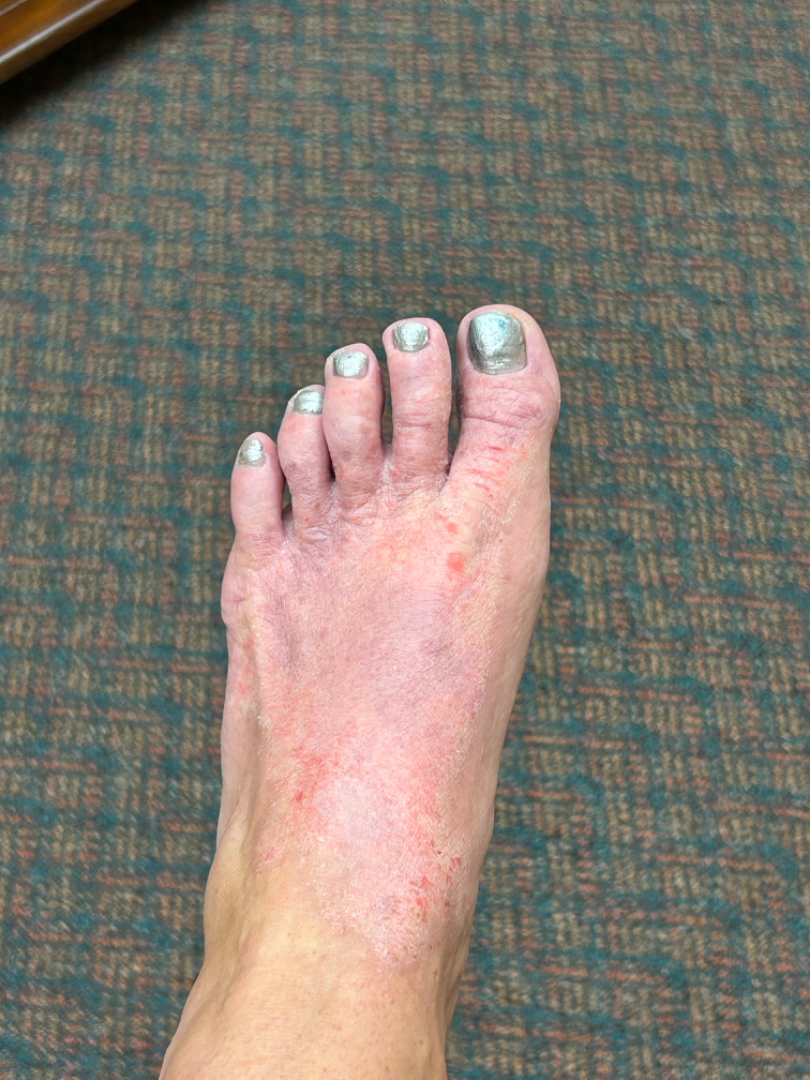<report>
  <skin_tone>
    <monk_skin_tone>2, 4</monk_skin_tone>
  </skin_tone>
  <shot_type>at a distance</shot_type>
  <duration>one to four weeks</duration>
  <symptoms>itching, bothersome appearance</symptoms>
  <patient>female, age 30–39</patient>
  <patient_category>a rash</patient_category>
  <body_site>arm, leg, top or side of the foot</body_site>
  <texture>rough or flaky, flat, raised or bumpy</texture>
  <differential>
    <leading>Allergic Contact Dermatitis</leading>
    <considered>Lichen Simplex Chronicus, Psoriasis</considered>
  </differential>
</report>